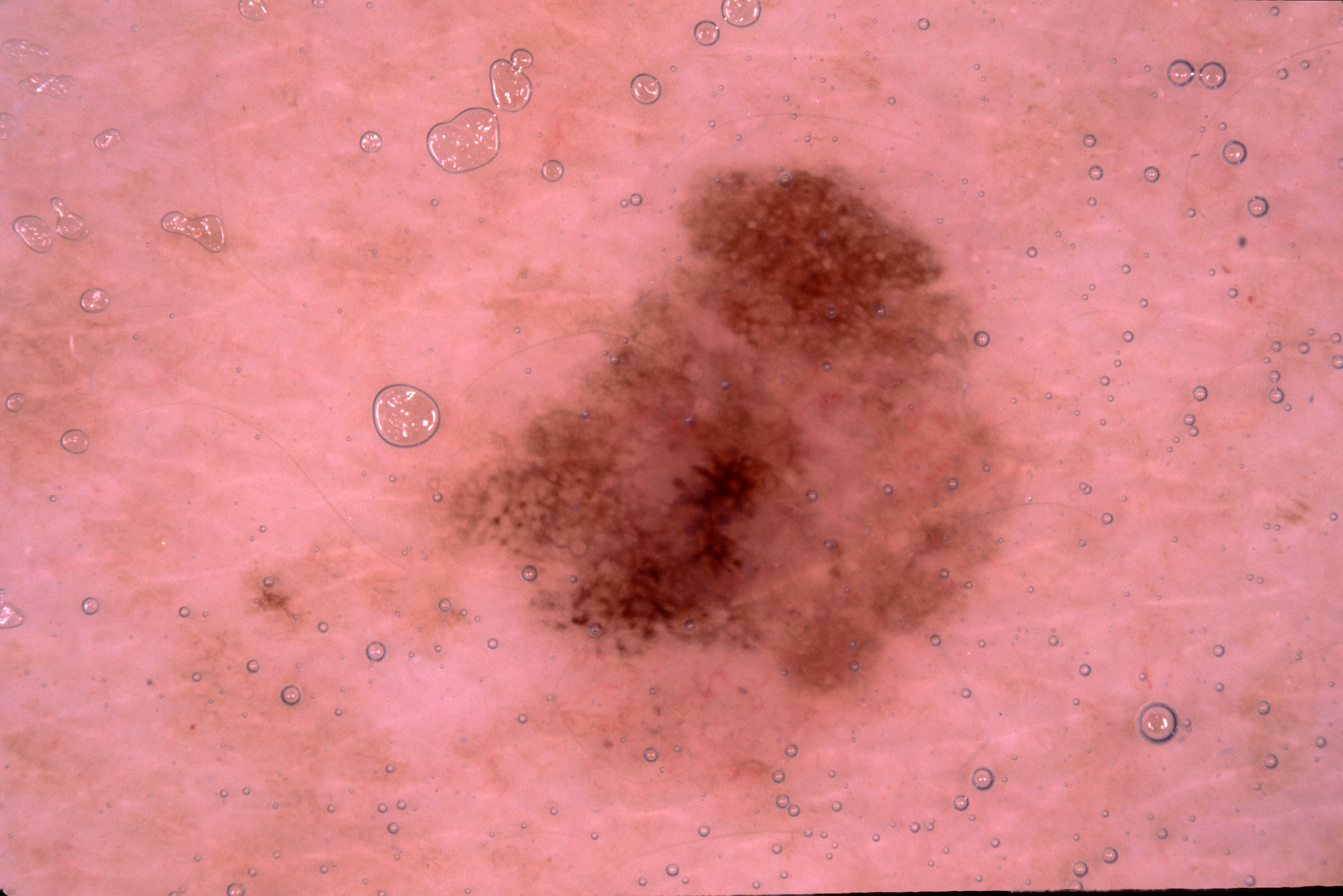Dermoscopy of a skin lesion. A female subject, in their 40s. The lesion's extent is [441, 168, 1018, 777]. Dermoscopic review identifies pigment network, with no streaks, milia-like cysts, or negative network. Histopathologically confirmed as a melanoma.